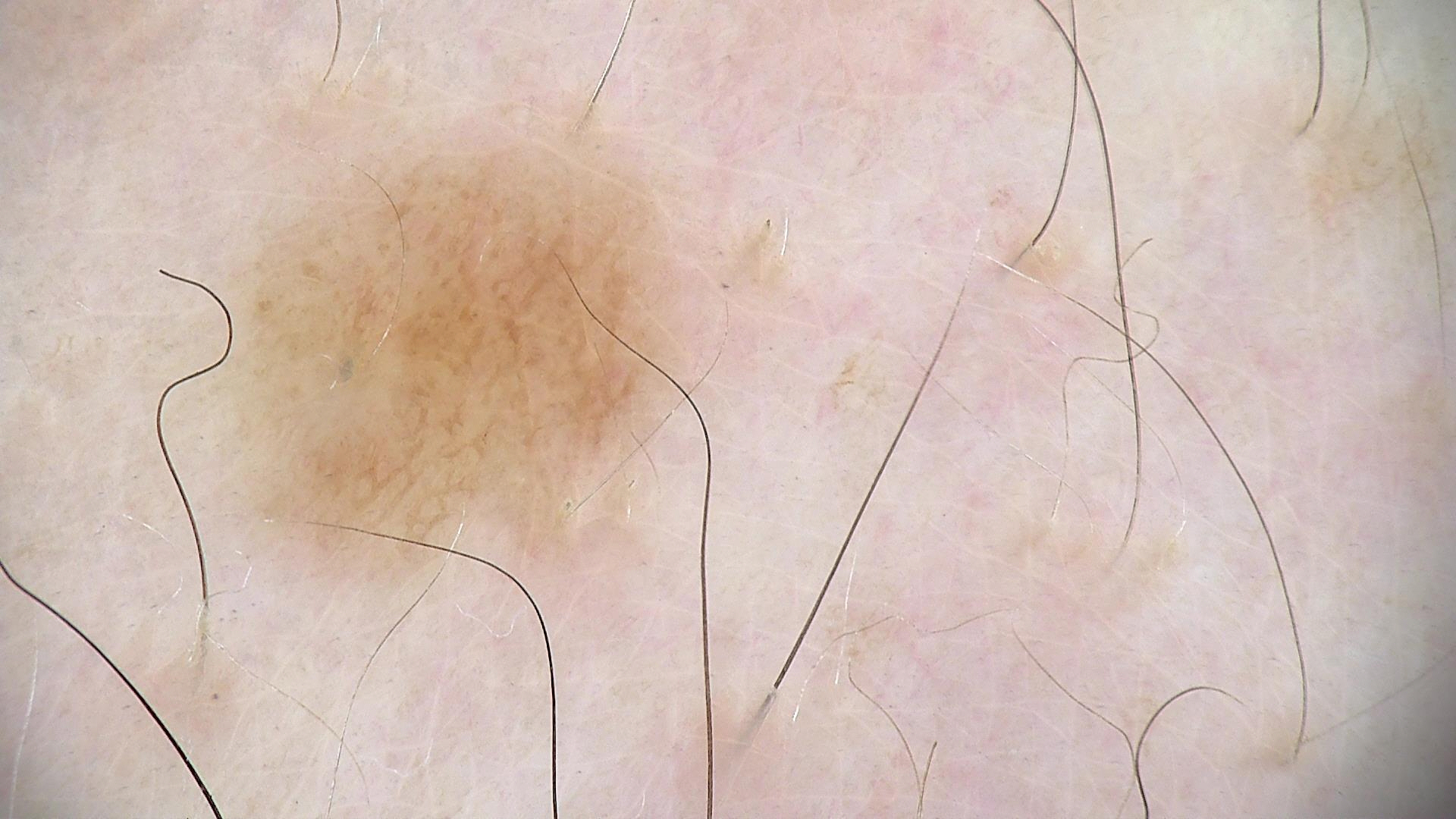Classified as a dysplastic junctional nevus.